A dermoscopic close-up of a skin lesion: 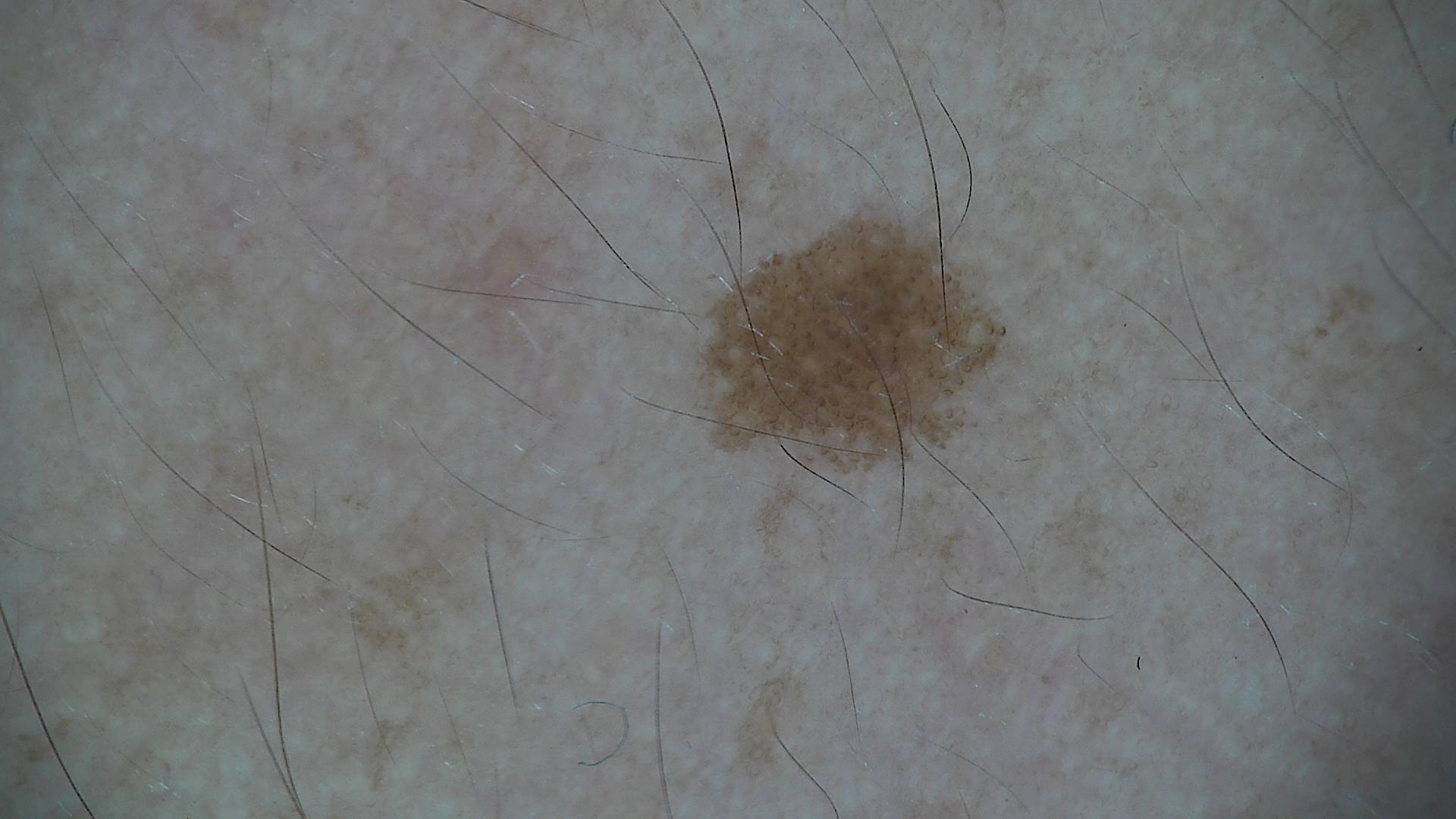{"diagnosis": {"name": "dysplastic junctional nevus", "code": "jd", "malignancy": "benign", "super_class": "melanocytic", "confirmation": "expert consensus"}}